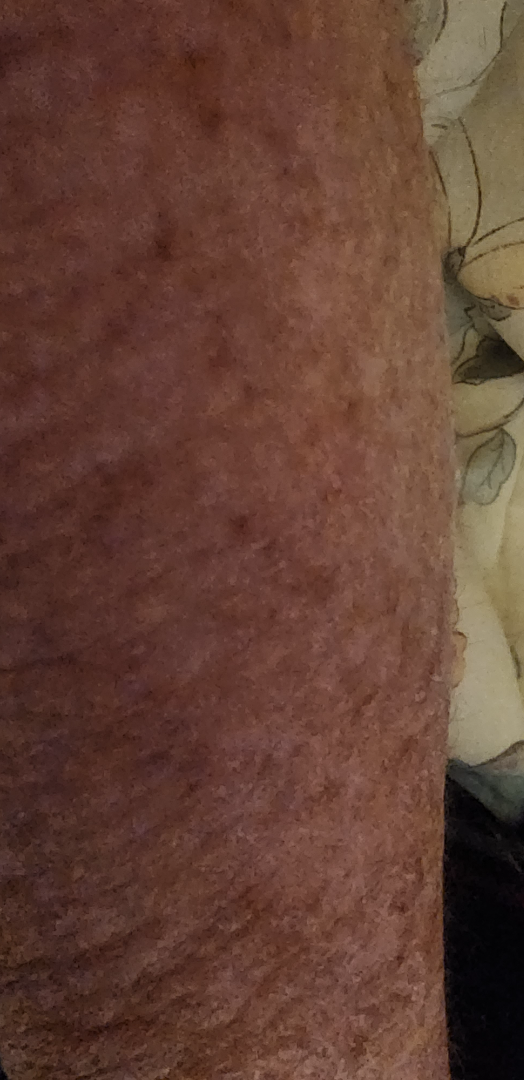<case>
<assessment>could not be assessed</assessment>
<patient>male, age 60–69</patient>
<shot_type>close-up</shot_type>
</case>